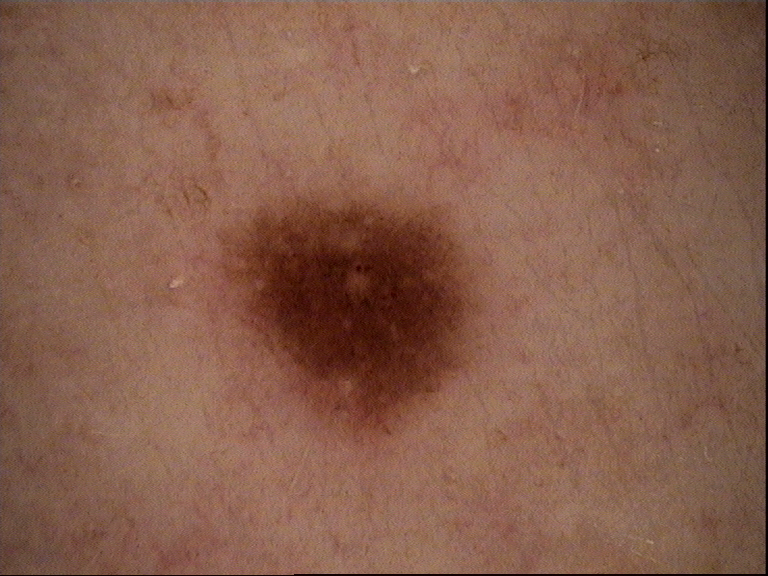{
  "image": "dermatoscopy",
  "diagnosis": {
    "name": "dysplastic junctional nevus",
    "code": "jd",
    "malignancy": "benign",
    "super_class": "melanocytic",
    "confirmation": "expert consensus"
  }
}